A dermoscopic close-up of a skin lesion:
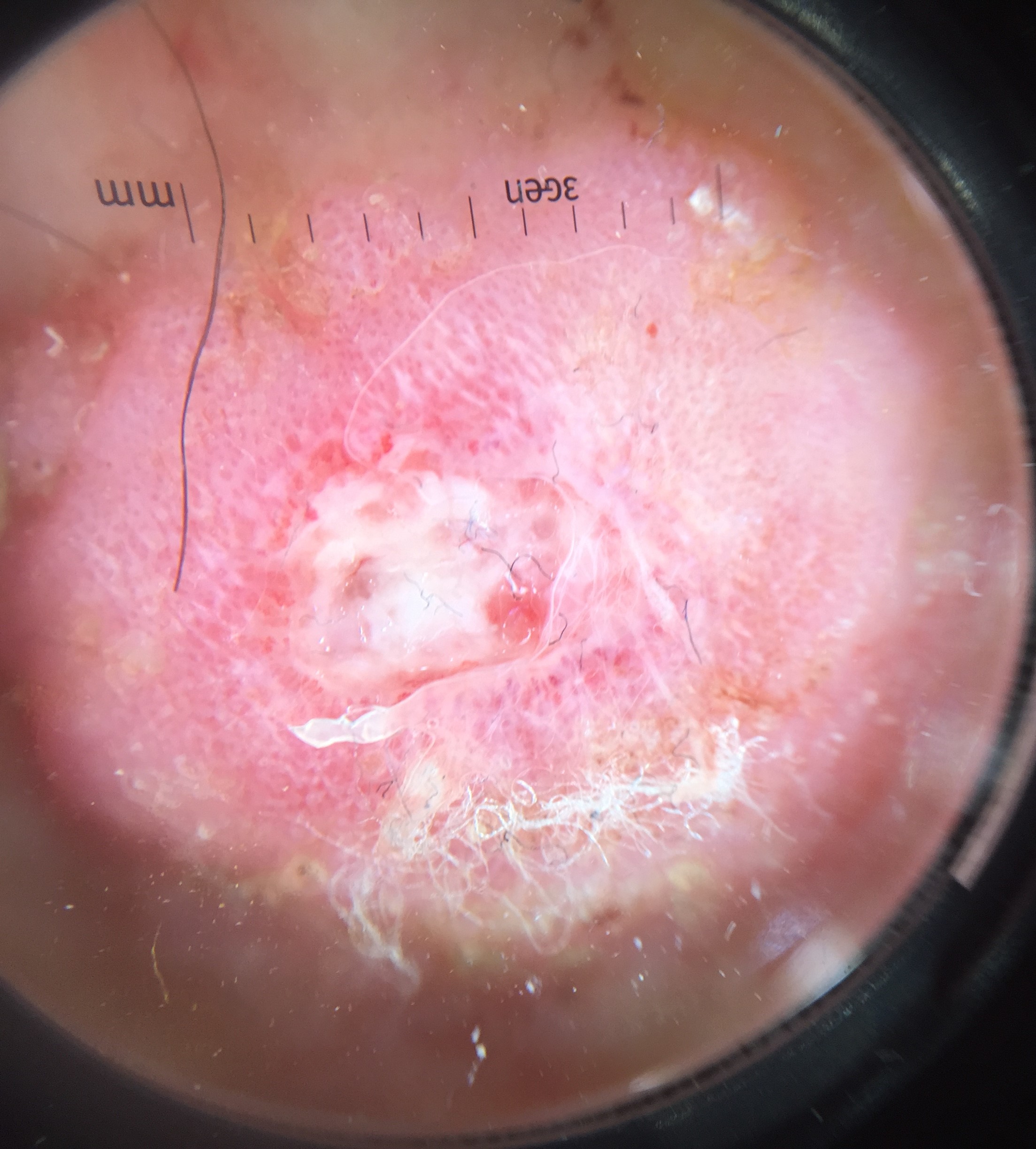The architecture is that of a keratinocytic lesion.
Biopsy-confirmed as a squamous cell carcinoma.